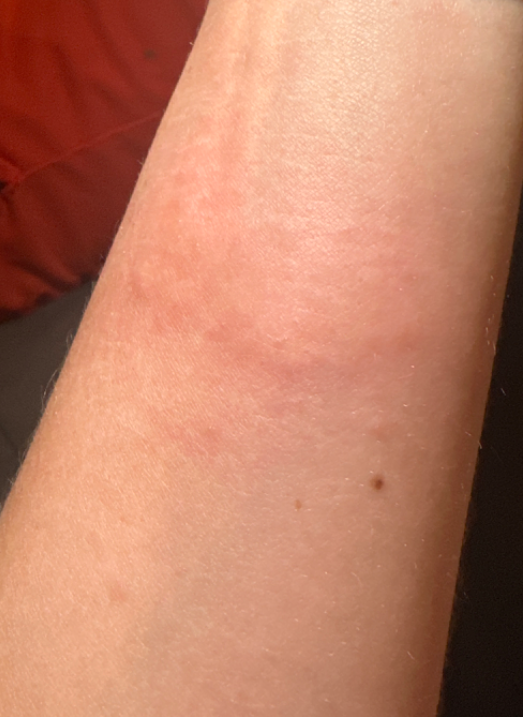Findings: The image was not sufficient for the reviewer to characterize the skin condition.